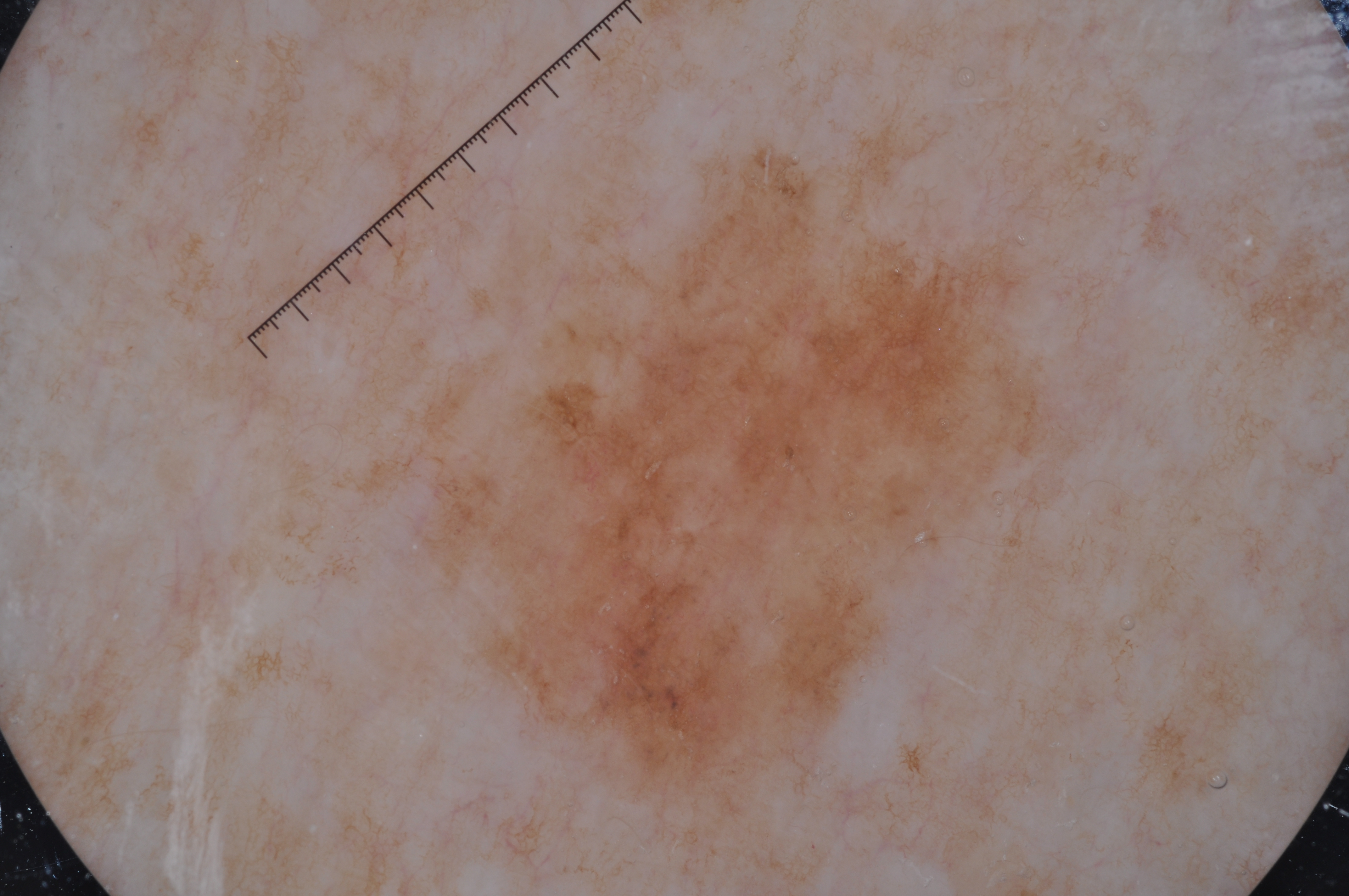subject = female, aged around 60 | image type = dermoscopic image | lesion extent = large | bounding box = box(327, 110, 1093, 847) | features = pigment network and milia-like cysts | diagnostic label = a melanoma, a malignant skin lesion.